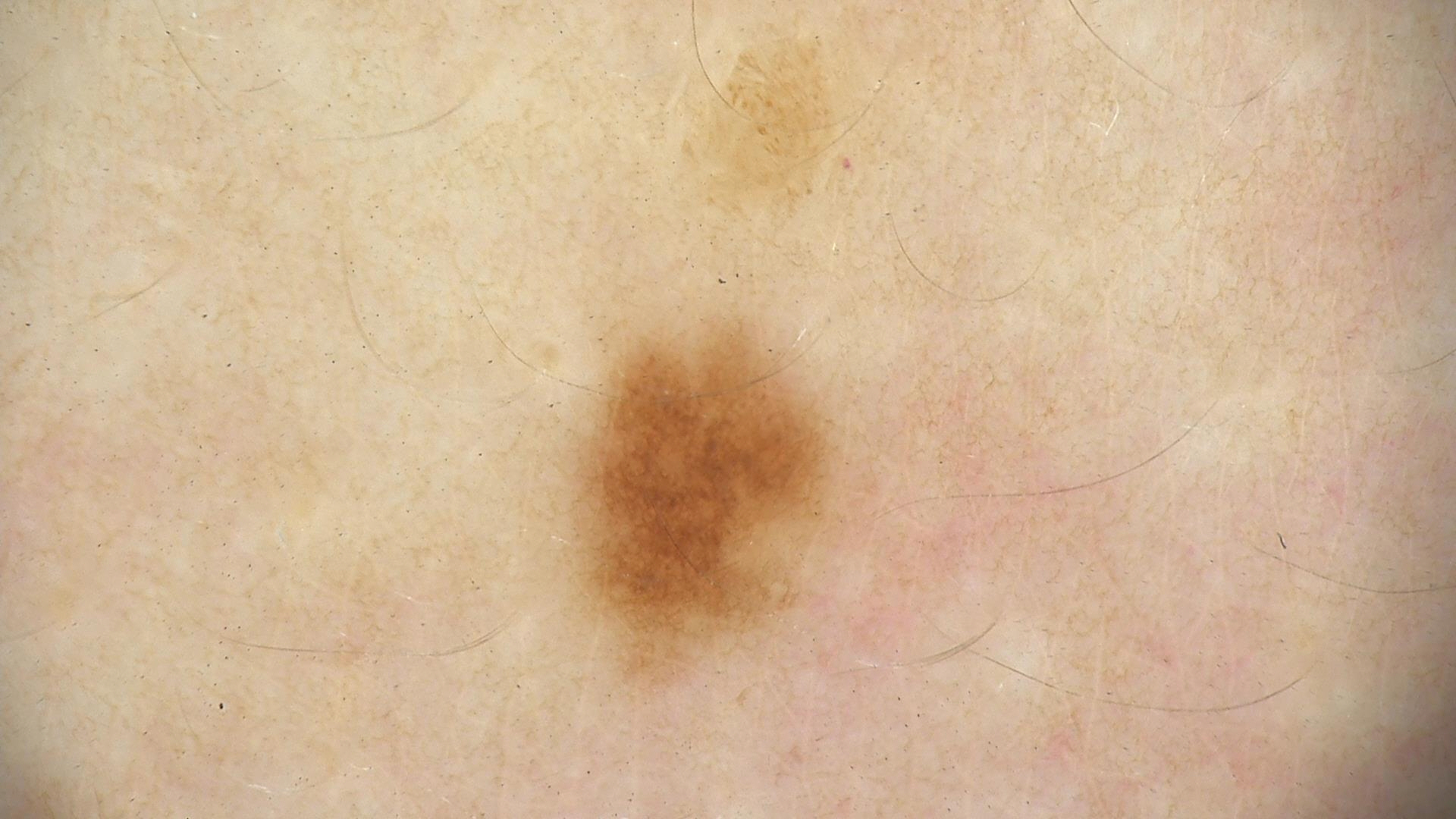| feature | finding |
|---|---|
| class | dysplastic junctional nevus (expert consensus) |